Dermoscopy of a skin lesion.
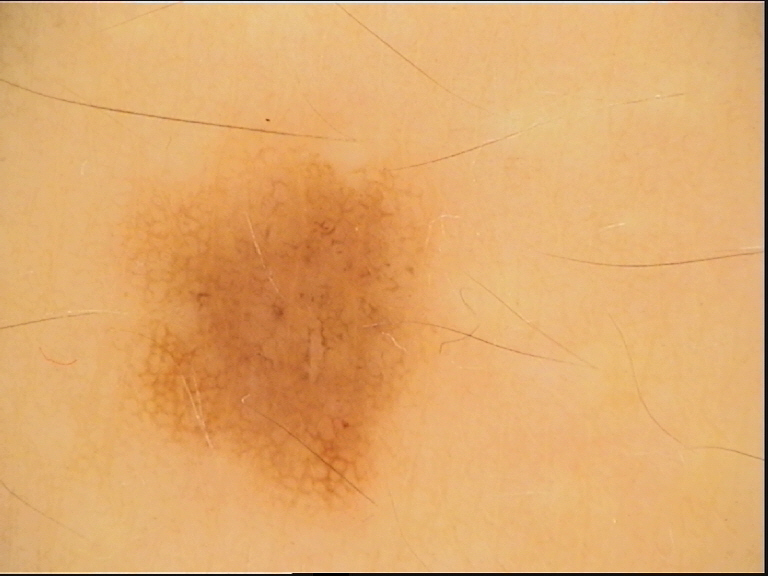Diagnosed as a dysplastic junctional nevus.